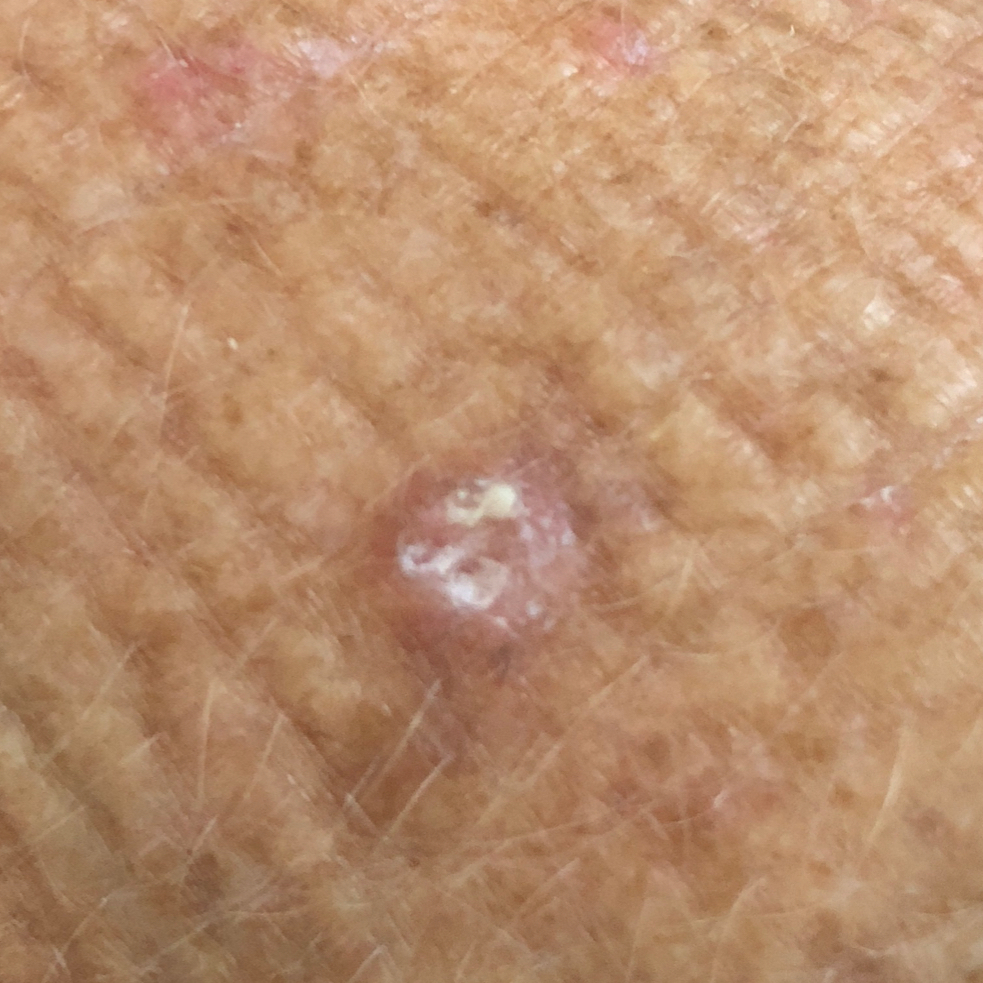Clinically diagnosed as an actinic keratosis.